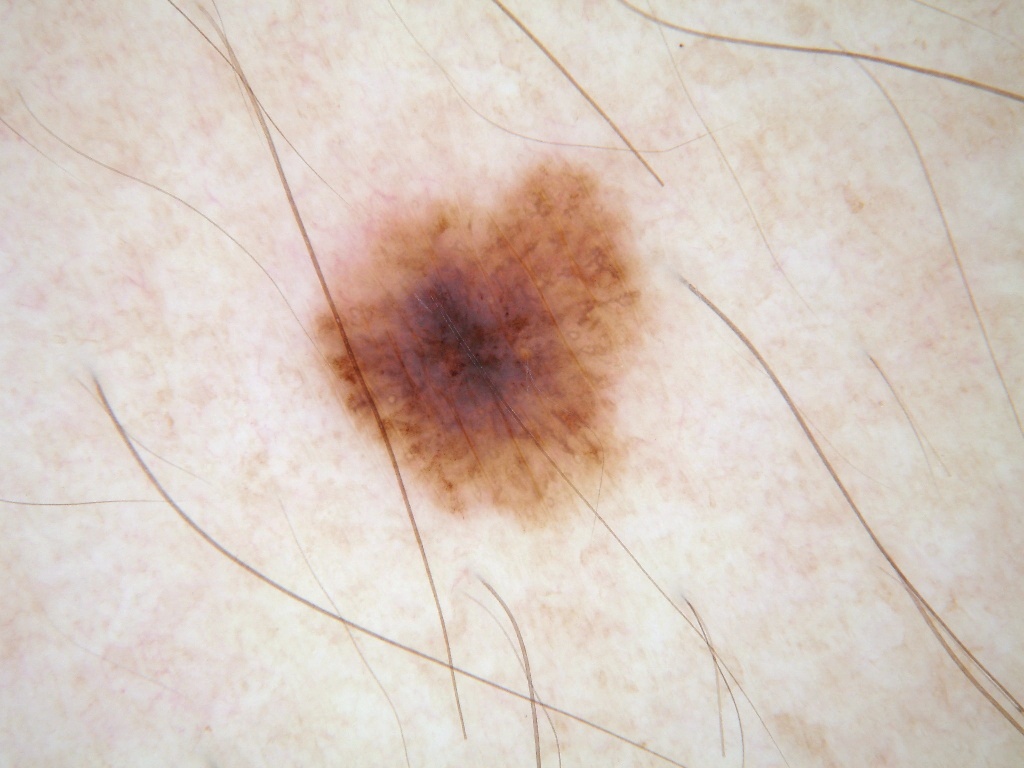Findings:
– patient · female, roughly 40 years of age
– imaging · dermoscopic image
– extent · moderate
– lesion bbox · 305 151 677 549
– dermoscopic features · pigment network
– diagnosis · a melanocytic nevus, a benign lesion